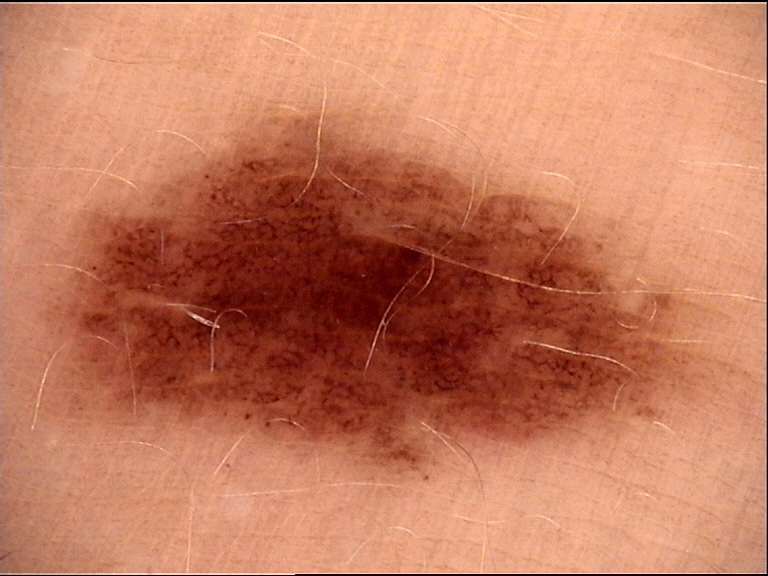A dermatoscopic image of a skin lesion. The diagnosis was a dysplastic junctional nevus.